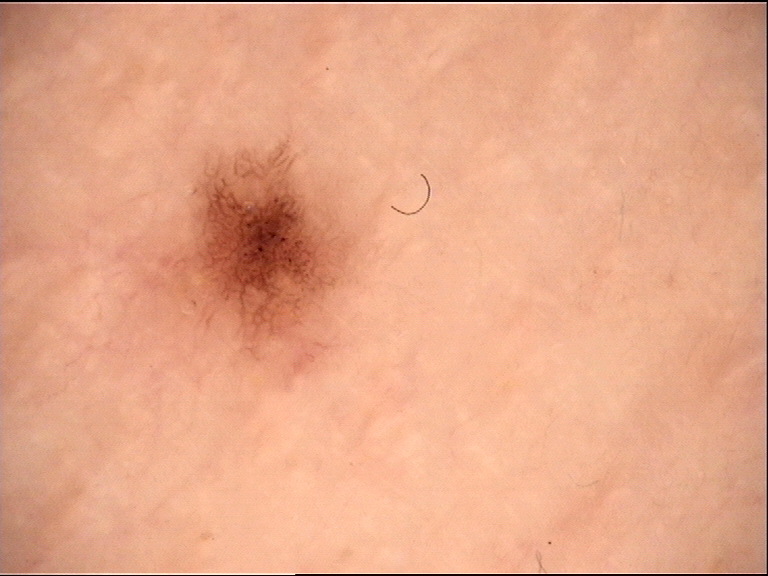{
  "diagnosis": {
    "name": "dysplastic junctional nevus",
    "code": "jd",
    "malignancy": "benign",
    "super_class": "melanocytic",
    "confirmation": "expert consensus"
  }
}